Recorded as Fitzpatrick skin type IV. History notes alcohol use and prior malignancy (patient or family): 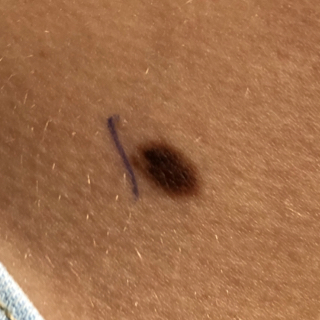region — the abdomen; symptoms — elevation, growth / no change in appearance, no itching; pathology — nevus (biopsy-proven).